A dermoscopic image of a skin lesion.
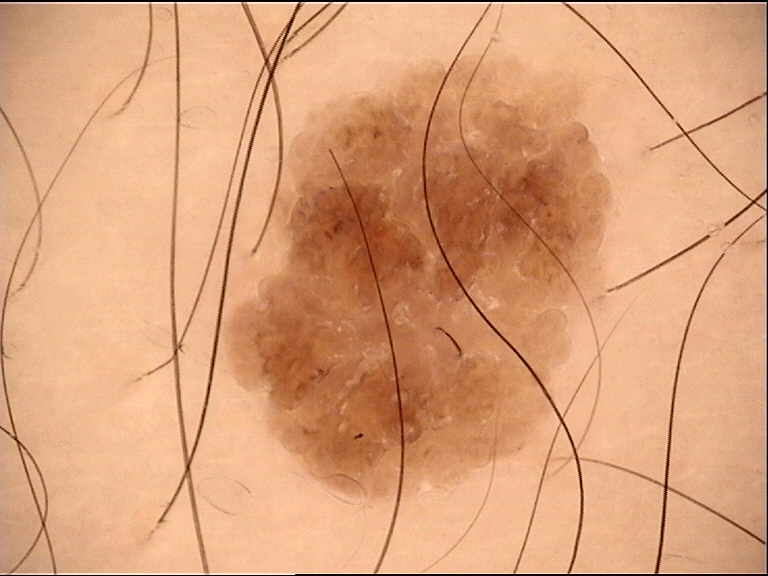Findings:
The morphology is that of a keratinocytic lesion.
Impression:
The diagnostic label was a seborrheic keratosis.